Dermoscopy of a skin lesion:
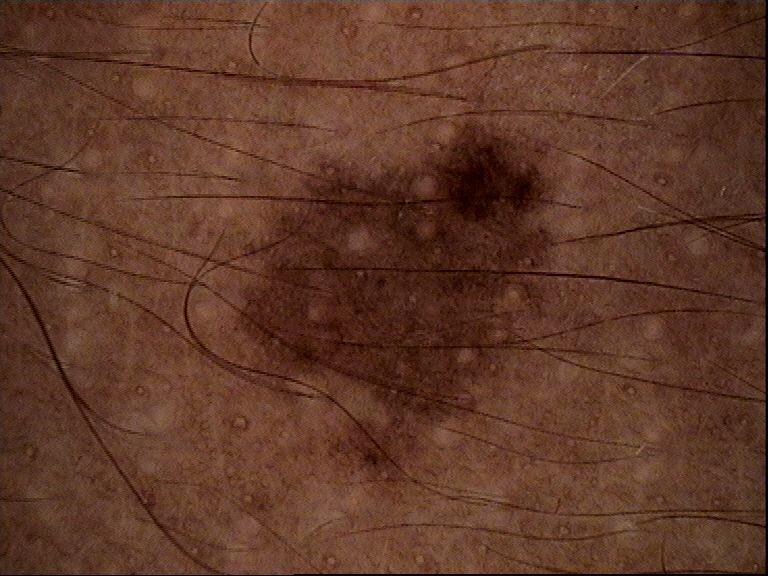  diagnosis:
    name: dysplastic junctional nevus
    code: jd
    malignancy: benign
    super_class: melanocytic
    confirmation: expert consensus